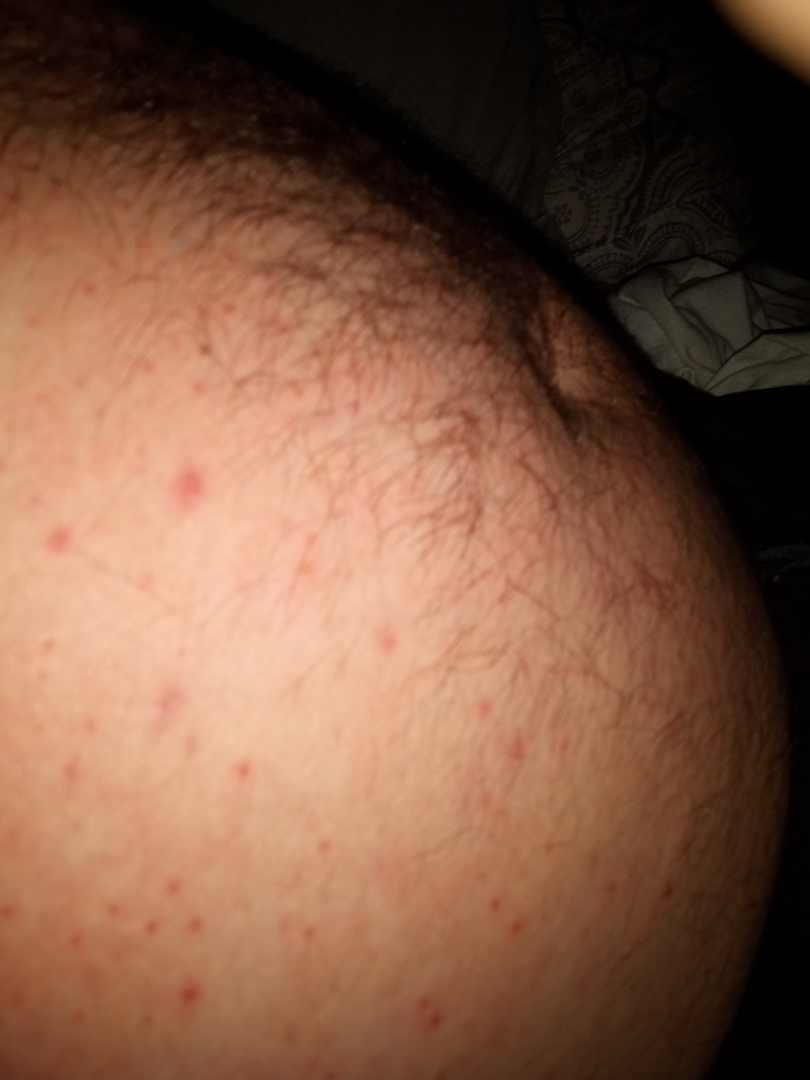- differential · the leading consideration is Scabies; less probable is Grover's disease; less likely is Folliculitis; a remote consideration is Drug Rash; a more distant consideration is Syphilis; lower on the differential is Pityriasis lichenoides